A dermatoscopic image of a skin lesion: 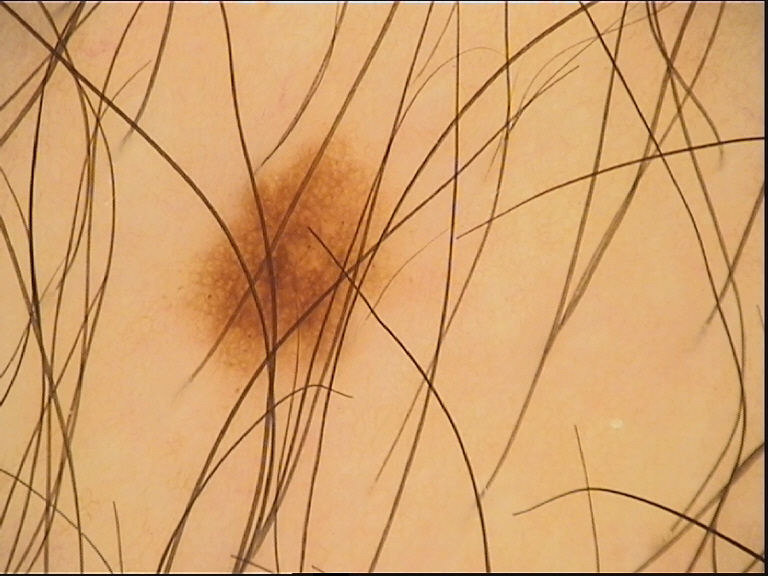The morphology is that of a banal lesion.
The diagnostic label was a junctional nevus.